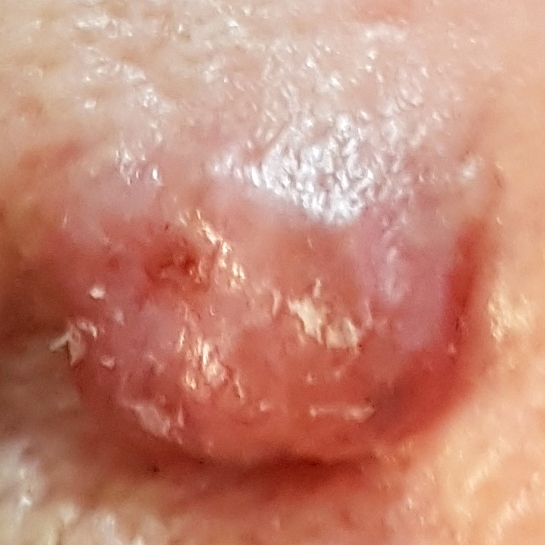Case:
- image type · clinical photo
- FST · II
- exposures · tobacco use
- subject · female, 86 years of age
- site · the nose
- size · 13 × 10 mm
- patient-reported symptoms · elevation, itching
- diagnosis · basal cell carcinoma (biopsy-proven)